Dermoscopy of a skin lesion.
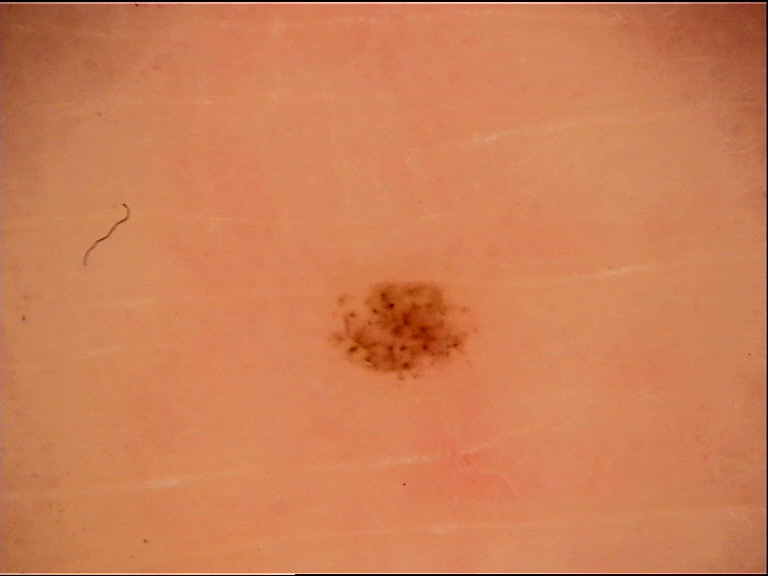Findings:
This is a banal lesion.
Impression:
Consistent with an acral junctional nevus.